A dermatoscopic image of a skin lesion.
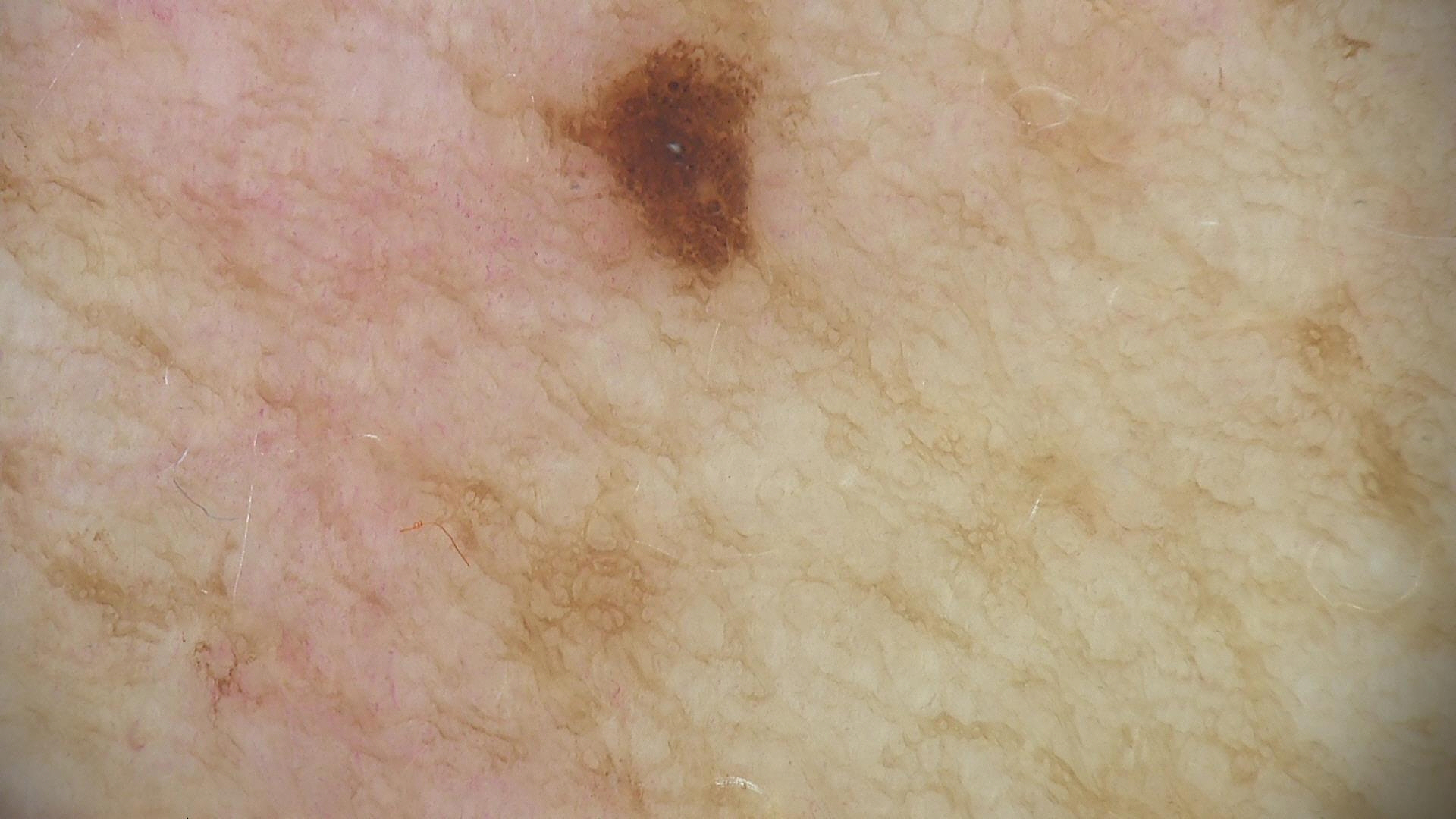Classified as a benign lesion — a dysplastic junctional nevus.